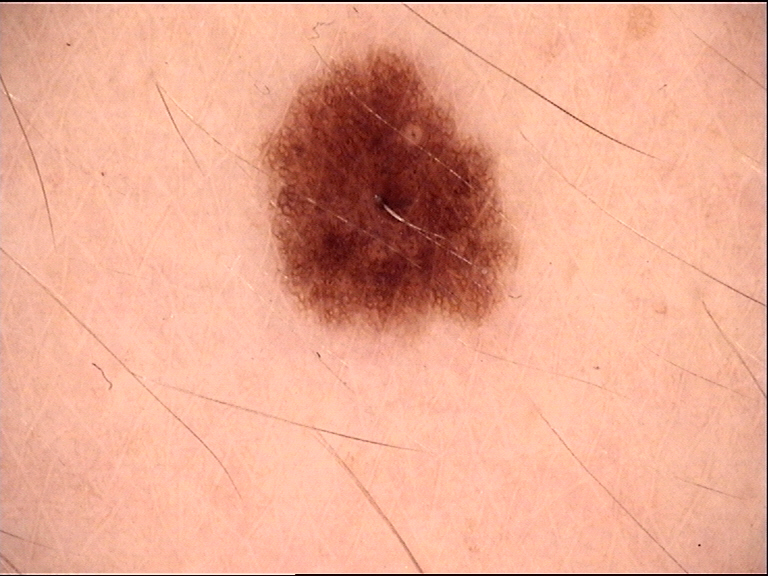Case: A dermoscopy image of a single skin lesion. Conclusion: Consistent with a dysplastic junctional nevus.